A dermoscopy image of a single skin lesion:
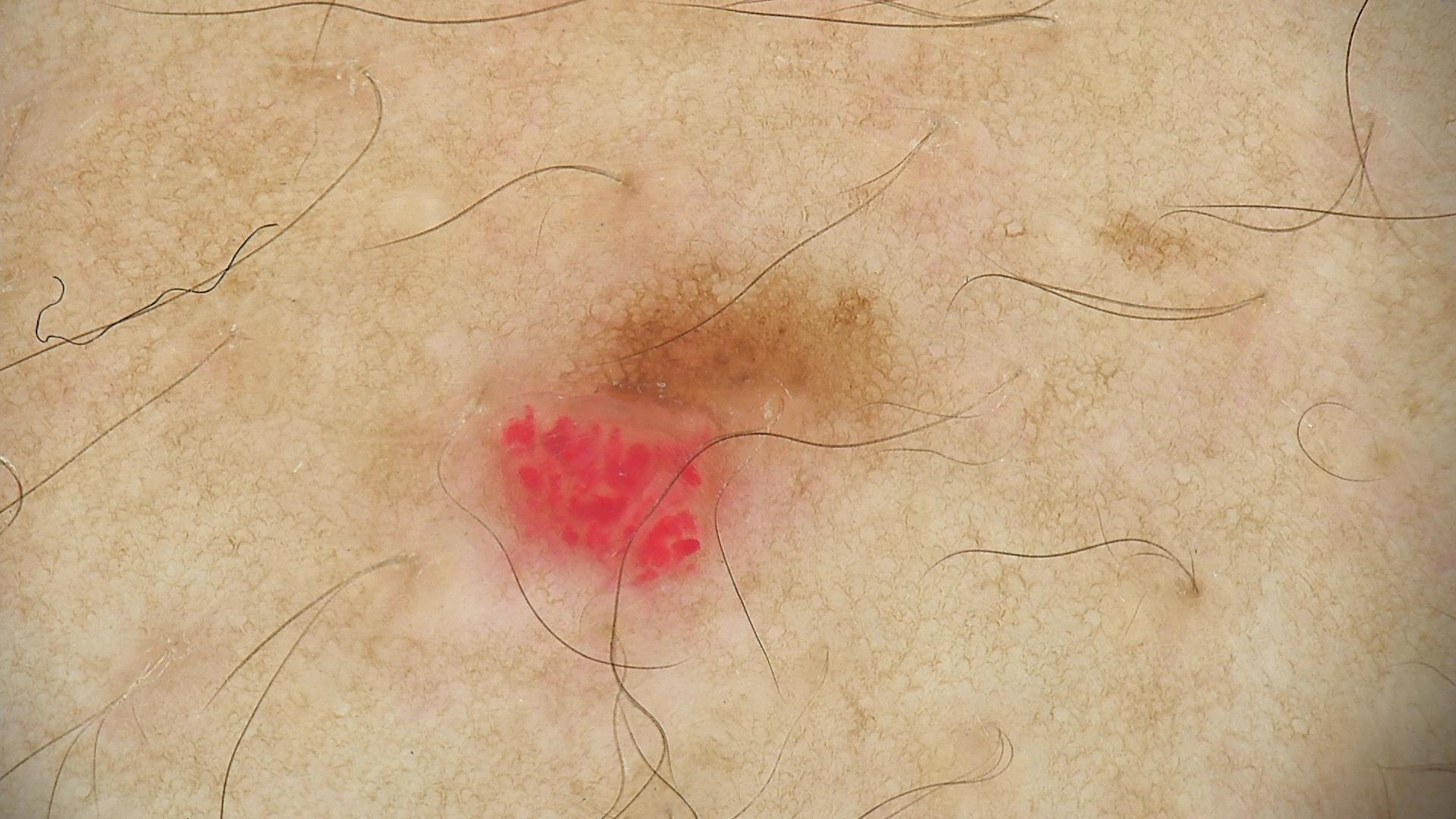category: vascular, diagnosis: hemangioma (expert consensus).